Close-up view: 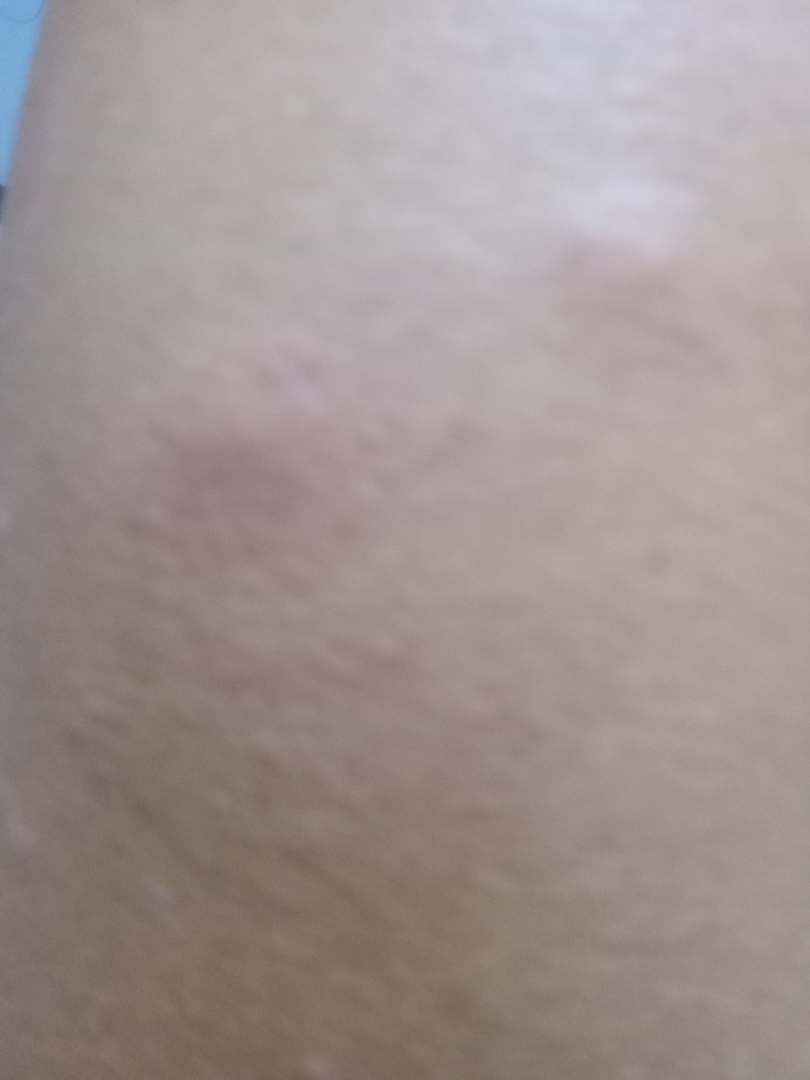The case was indeterminate on photographic review.